Close-up view; the lesion involves the leg; the patient is 40–49, female: 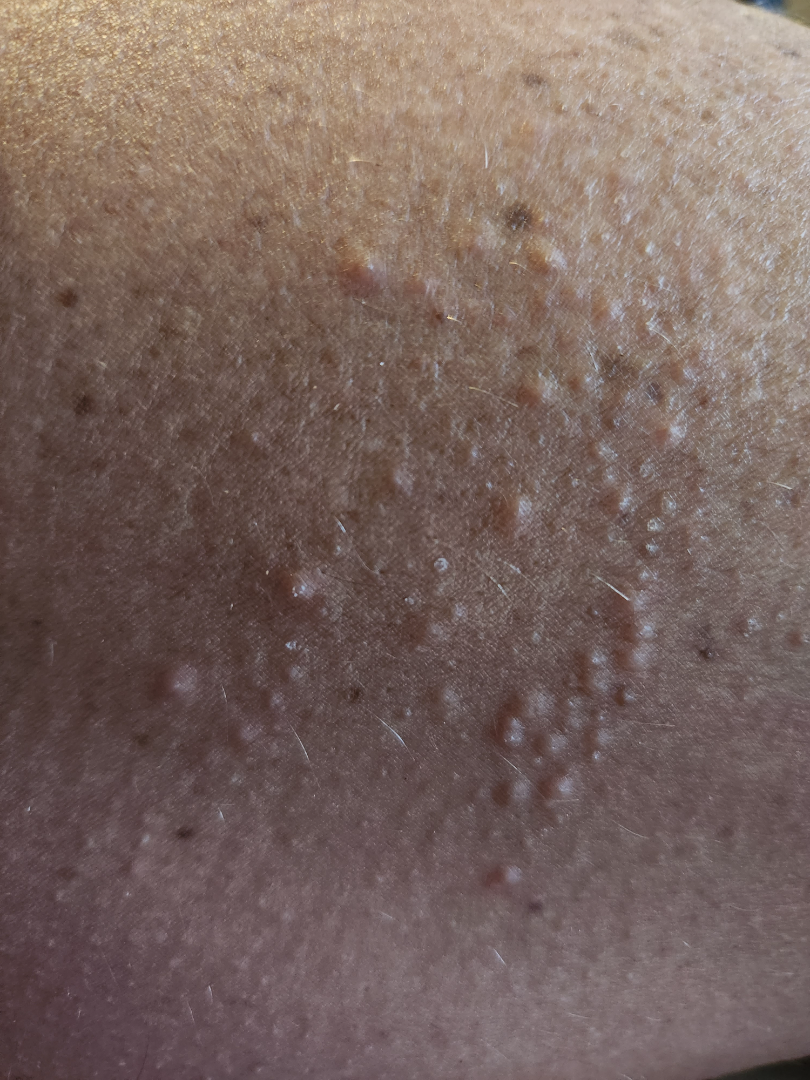Findings: On photographic review, the leading consideration is Folliculitis; possibly Keratosis pilaris; also raised was Lichen spinulosus.